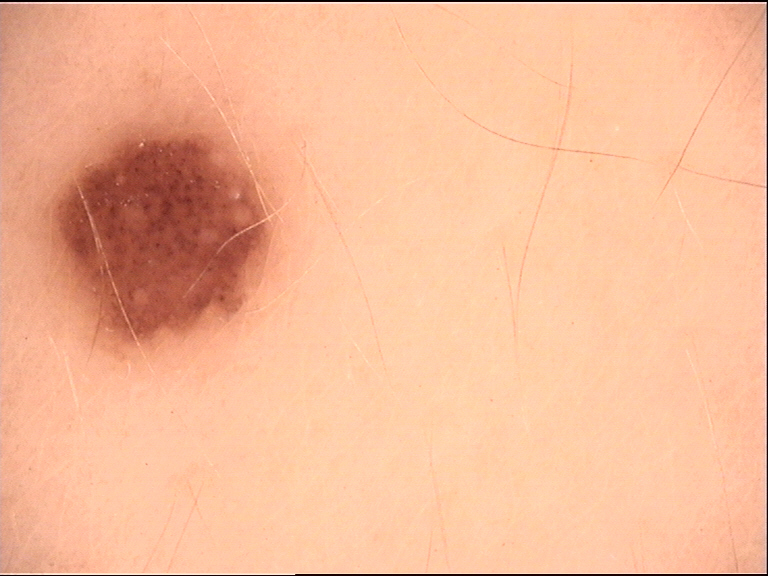The diagnosis was a benign lesion — a dysplastic junctional nevus.